Dermoscopy of a skin lesion · the chart notes a previous melanoma · recorded as Fitzpatrick II:
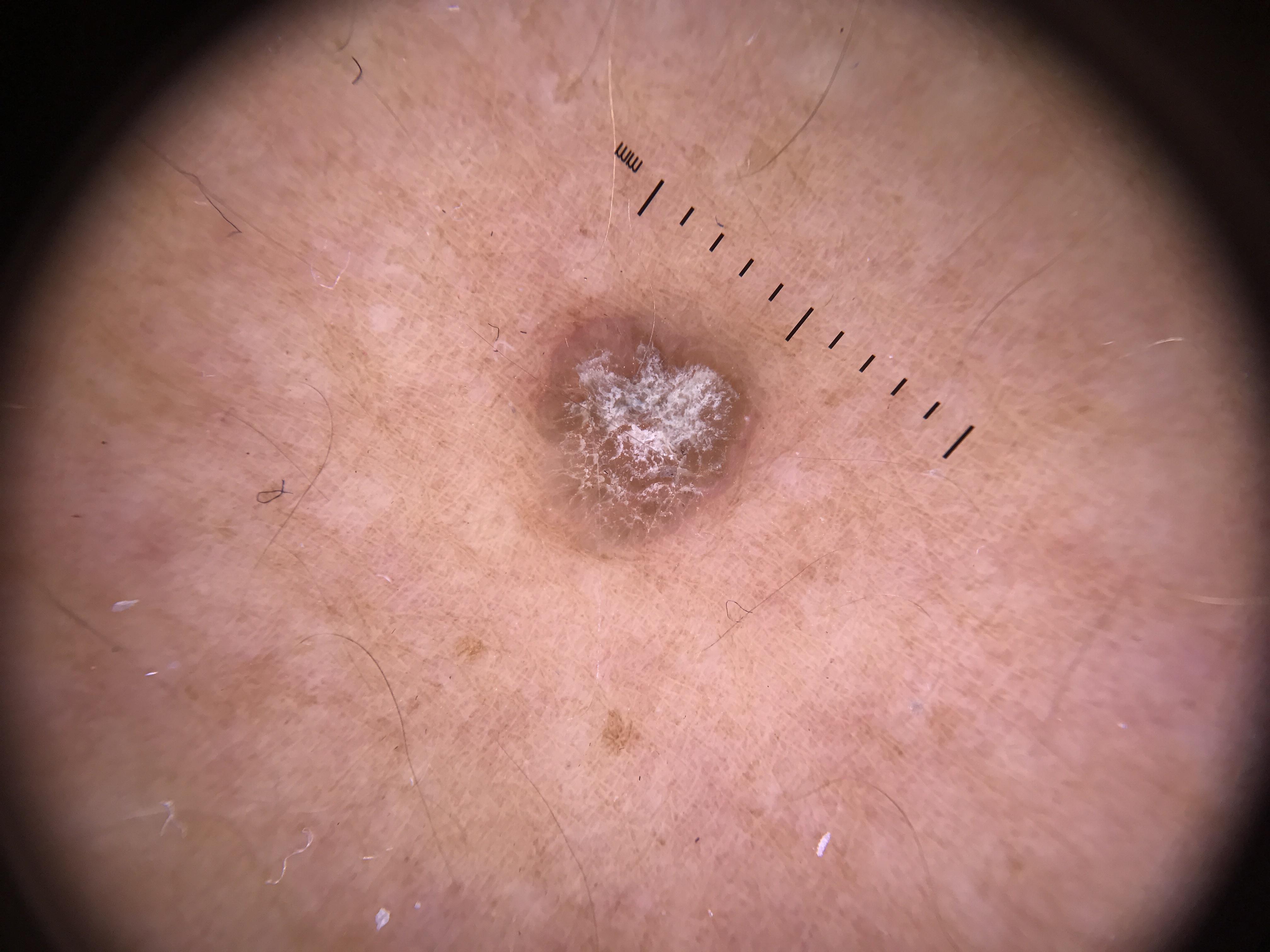Located on a lower extremity. Consistent with an epidermal lesion — a seborrheic keratosis.